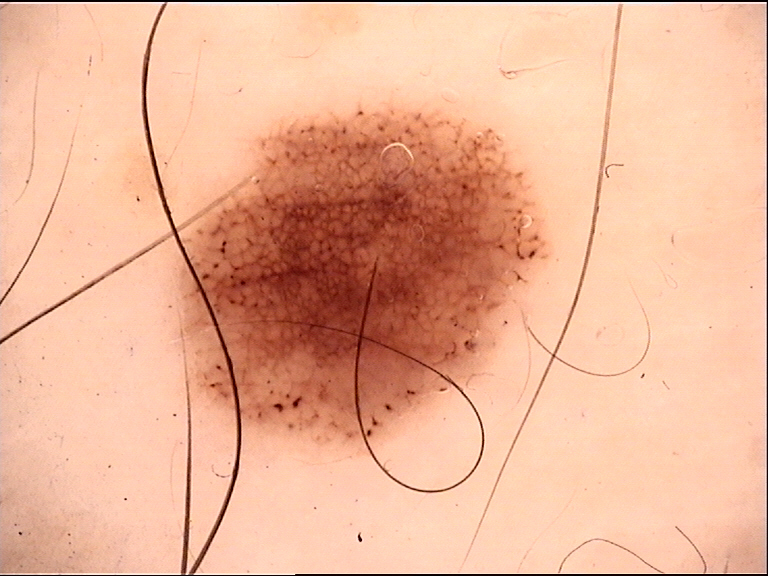class: dysplastic junctional nevus (expert consensus)